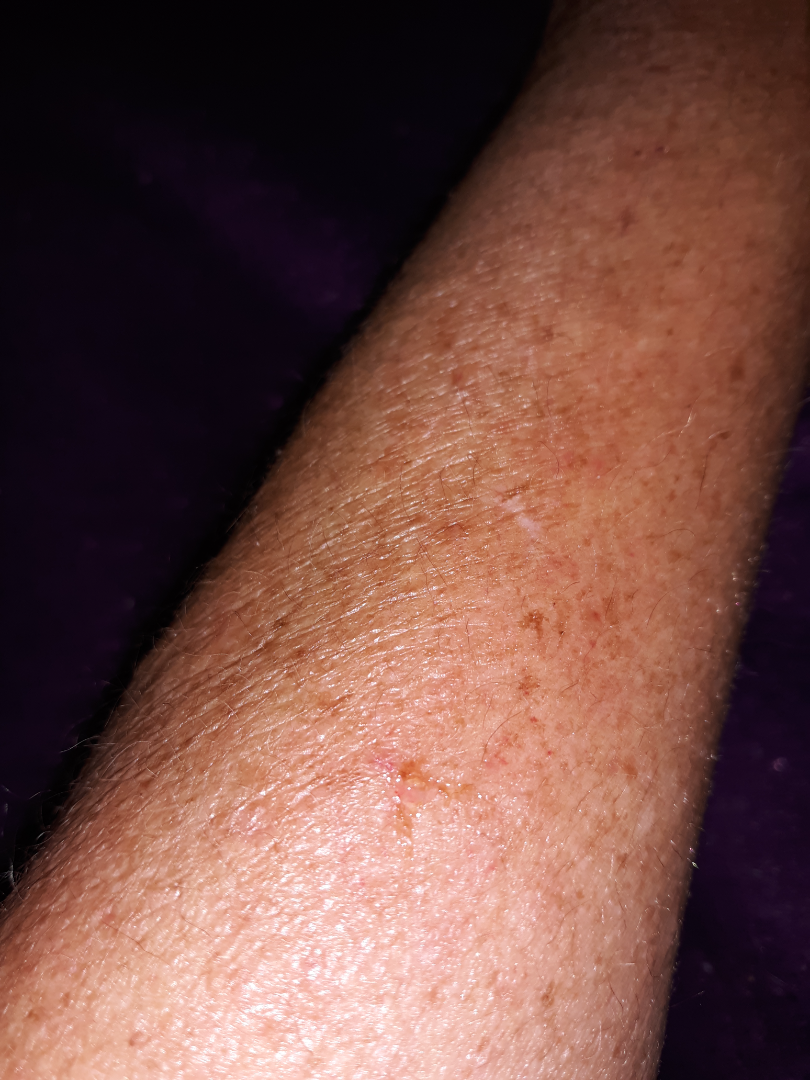photo taken=close-up.